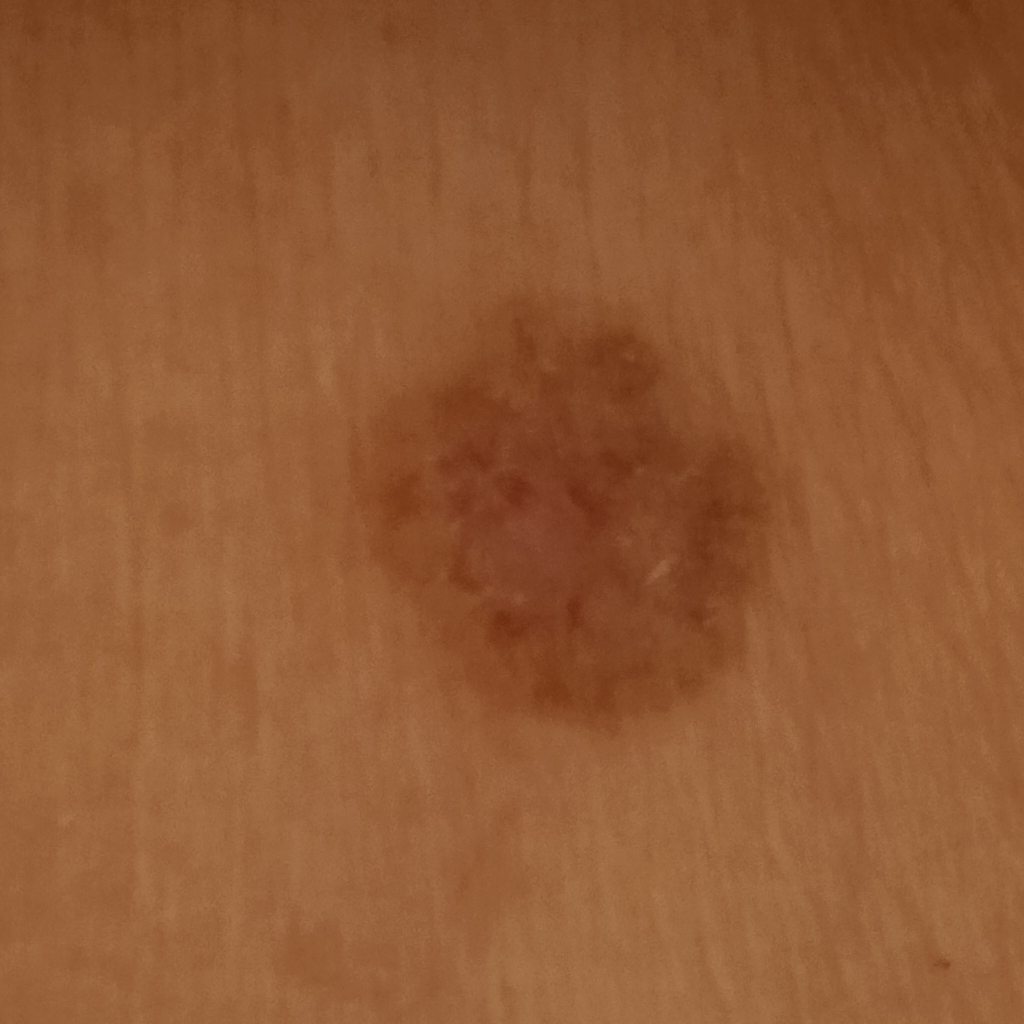The diagnostic impression was a basal cell carcinoma.